This image was taken at an angle; the contributor is 30–39, female; the affected area is the leg.
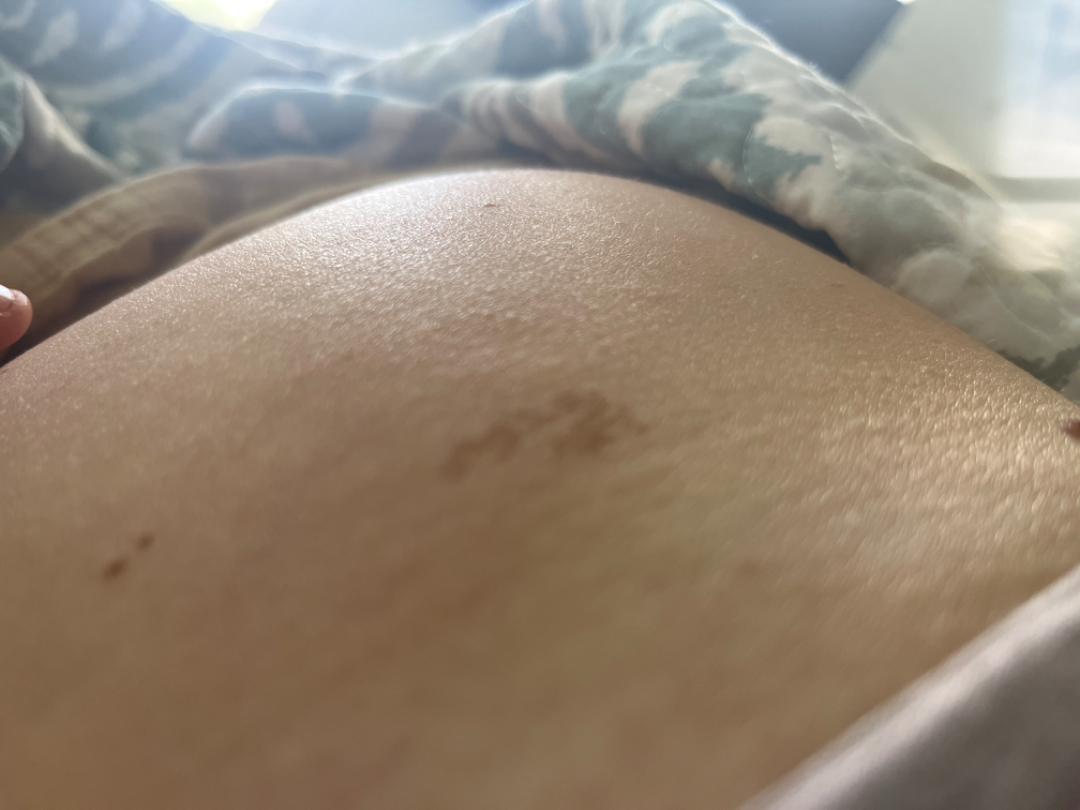assessment = could not be assessed, texture = flat, onset = since childhood, self-categorized as = a pigmentary problem, reported symptoms = none reported.